A skin lesion imaged with a dermatoscope — 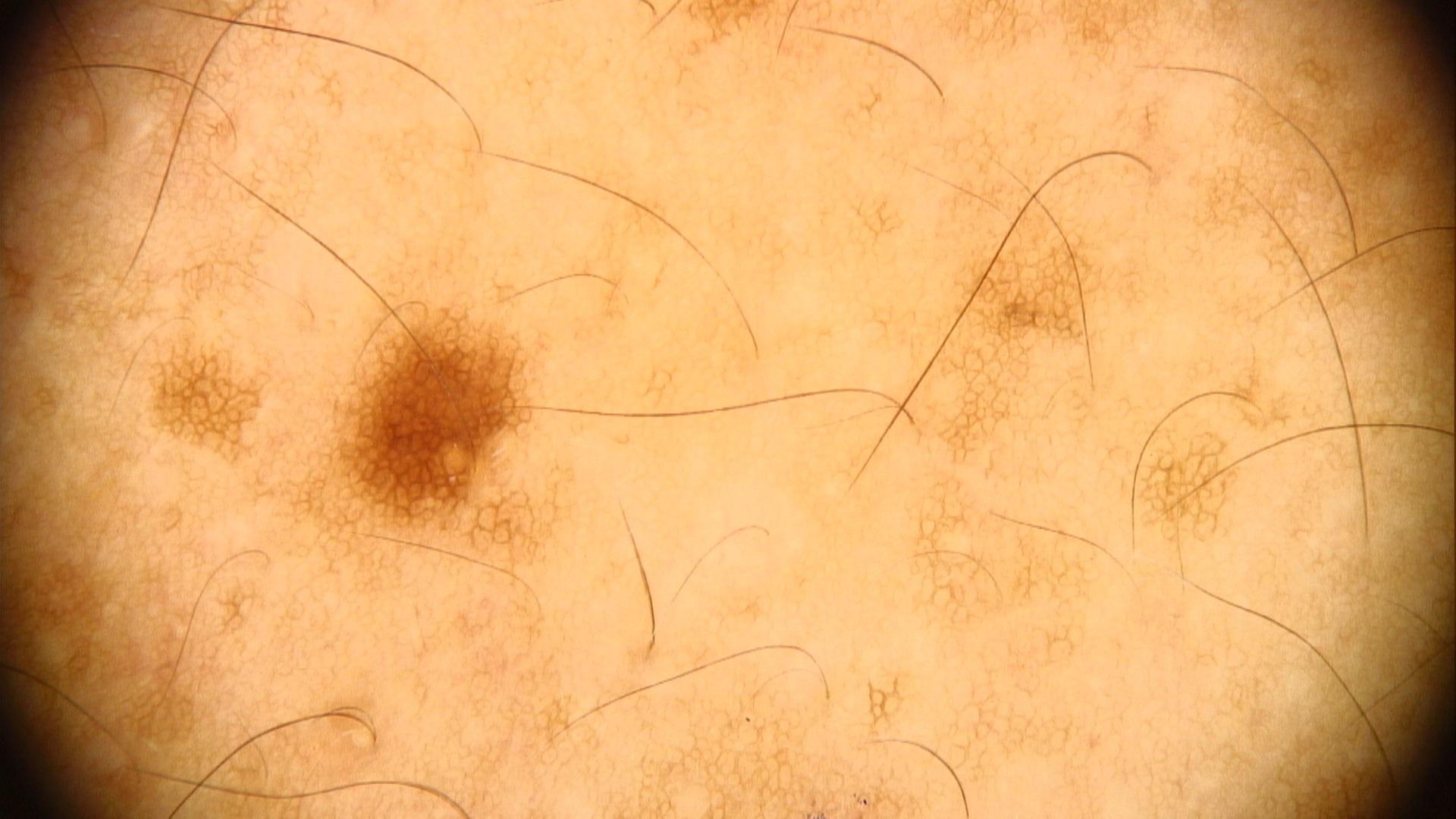The lesion is on the trunk.
The clinical assessment was a benign, melanocytic lesion — a nevus.